A dermoscopic photograph of a skin lesion: 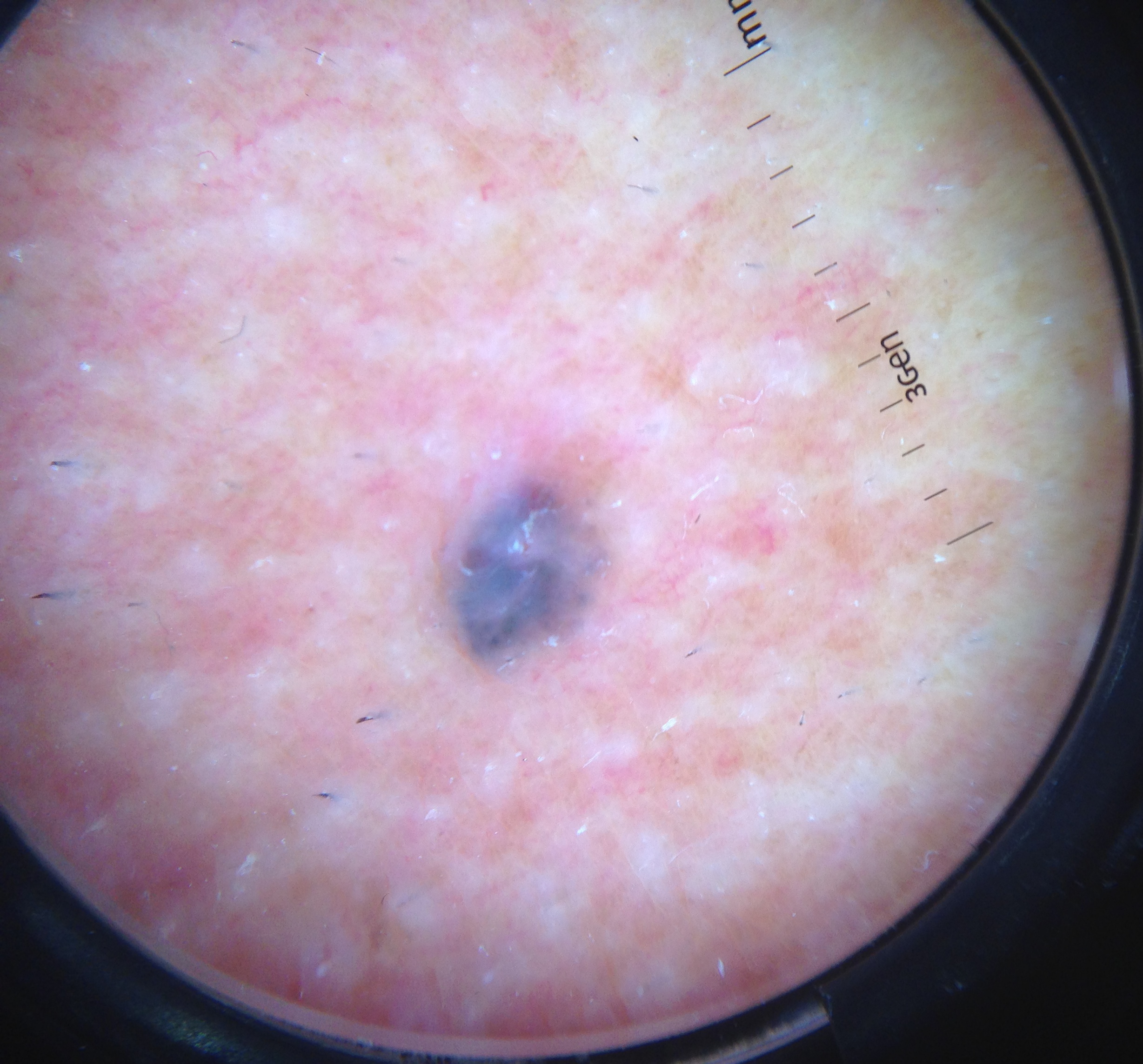• diagnosis: basal cell carcinoma (biopsy-proven)